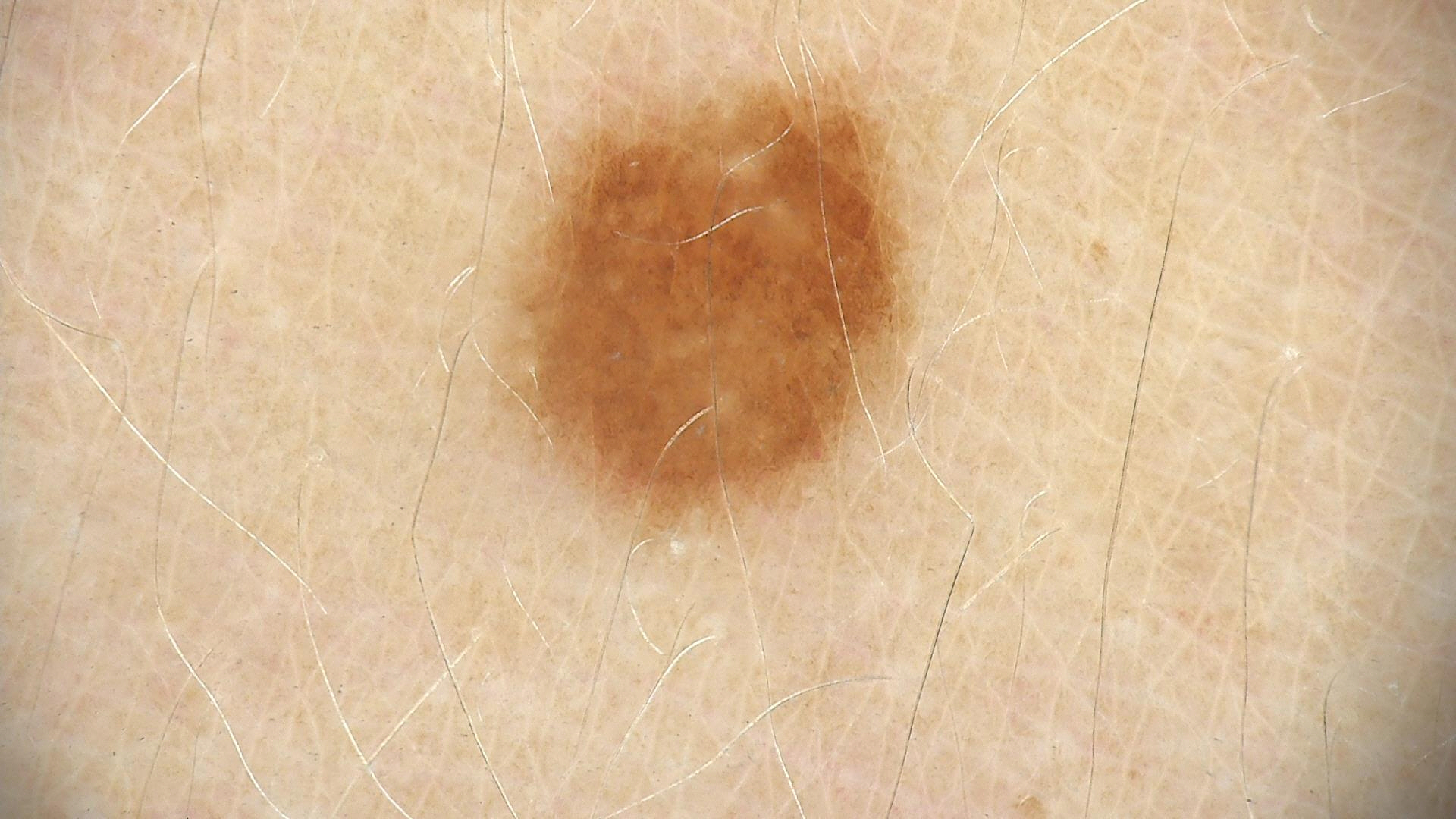Labeled as a benign lesion — a dysplastic junctional nevus.